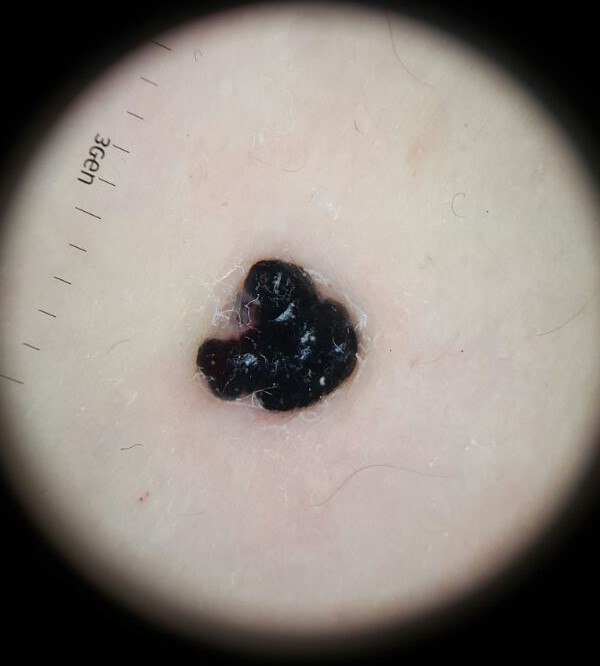Conclusion: Consistent with a benign lesion — an angiokeratoma.